The patient was assessed as Fitzpatrick phototype III · a male subject approximately 40 years of age: 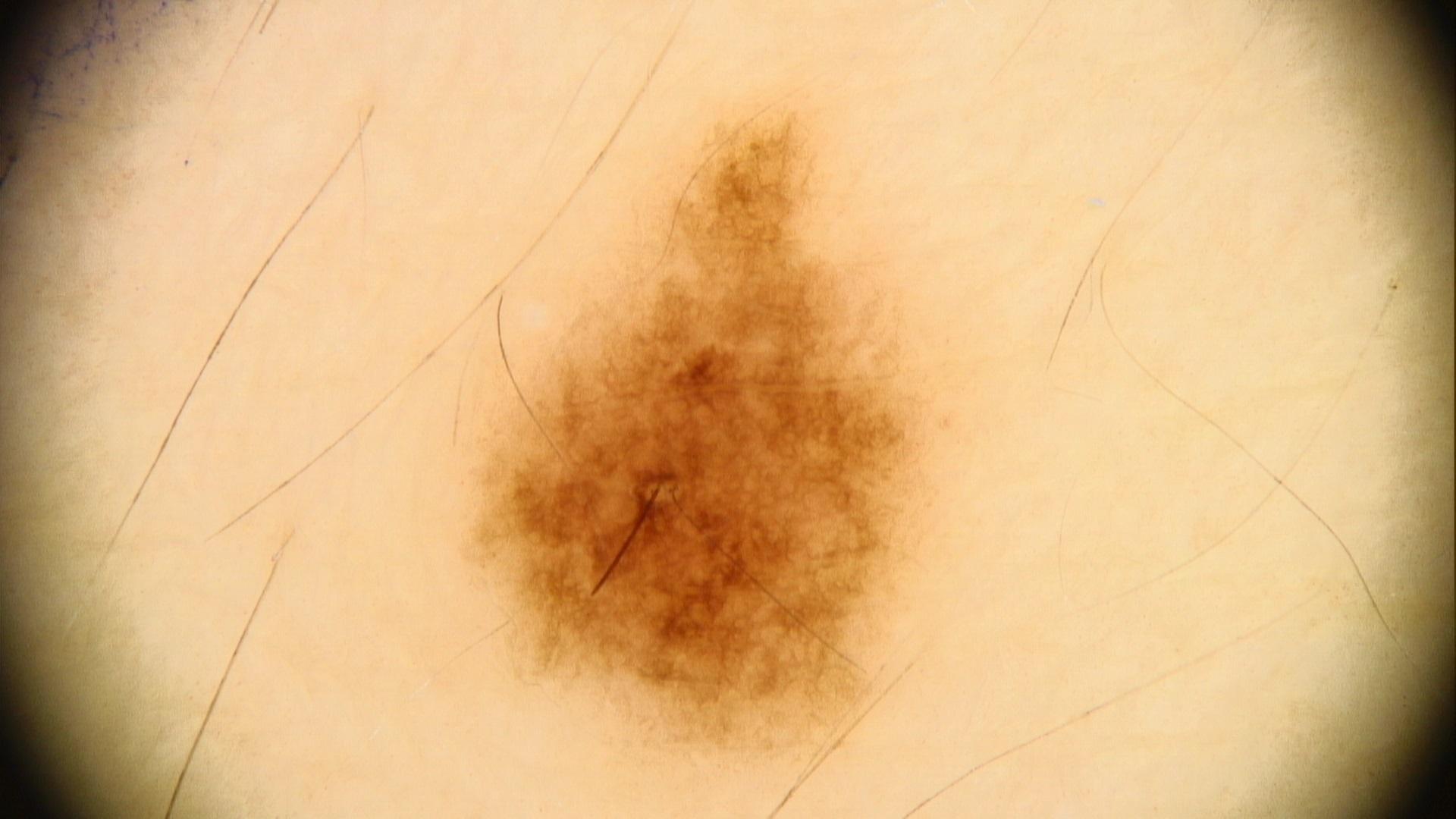The lesion is located on the trunk. The clinical assessment was a lesion of melanocytic lineage — a nevus.